Fitzpatrick IV. The photograph is a close-up of the affected area.
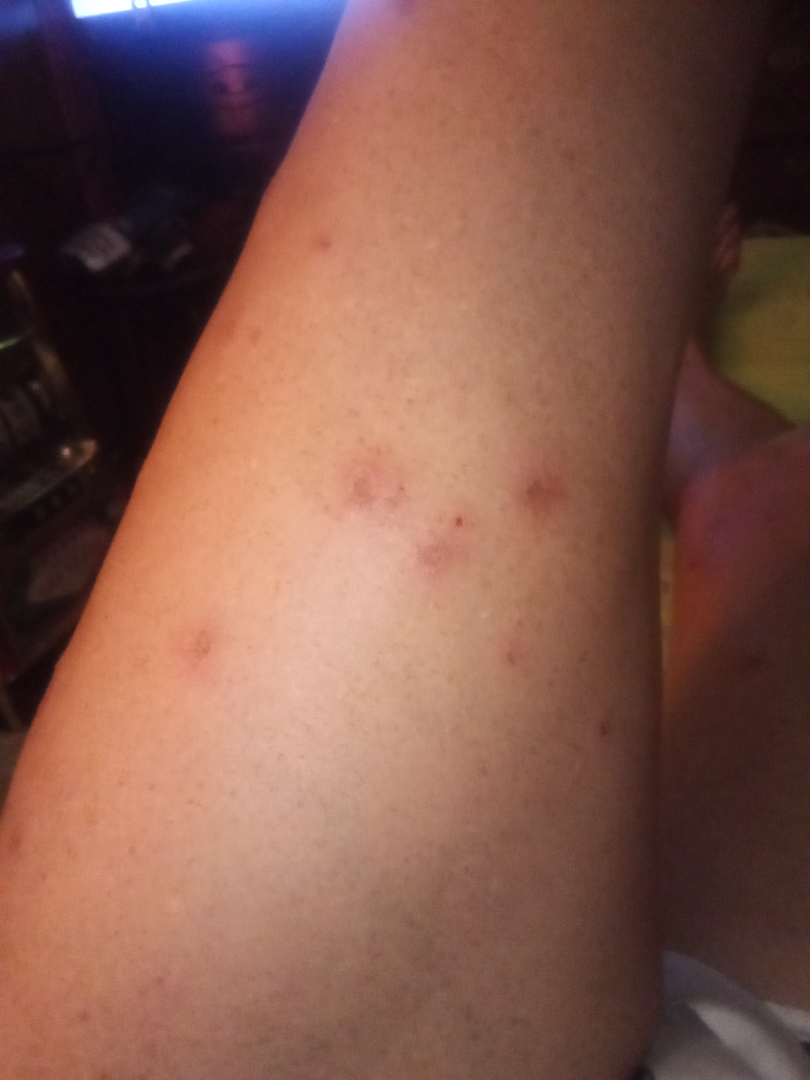Notes:
* impression · the differential, in no particular order, includes Folliculitis and Insect Bite